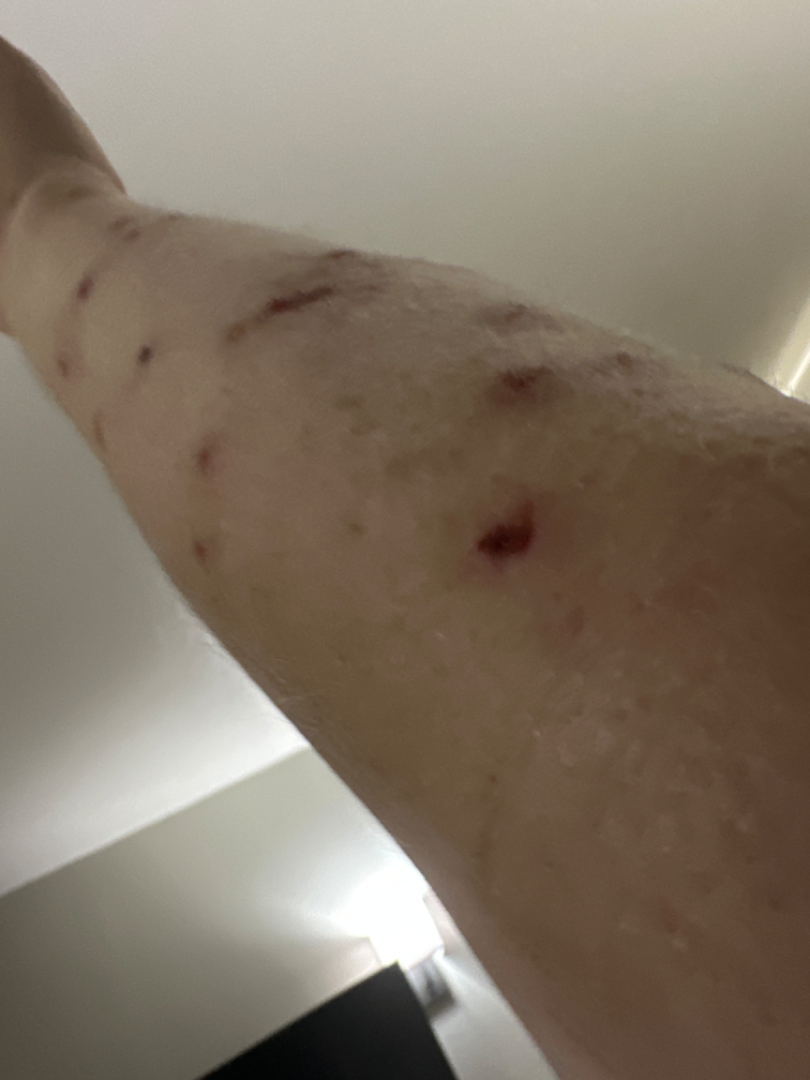Clinical context:
The lesion involves the head or neck, arm, back of the hand, leg, front of the torso and back of the torso. The lesion is described as rough or flaky and raised or bumpy. The photo was captured at a distance. The patient notes associated fatigue and joint pain. The patient considered this a rash. The lesion is associated with bleeding, bothersome appearance and itching. Reported duration is three to twelve months. The subject is female.
Assessment:
A single dermatologist reviewed the case: in keeping with Prurigo.